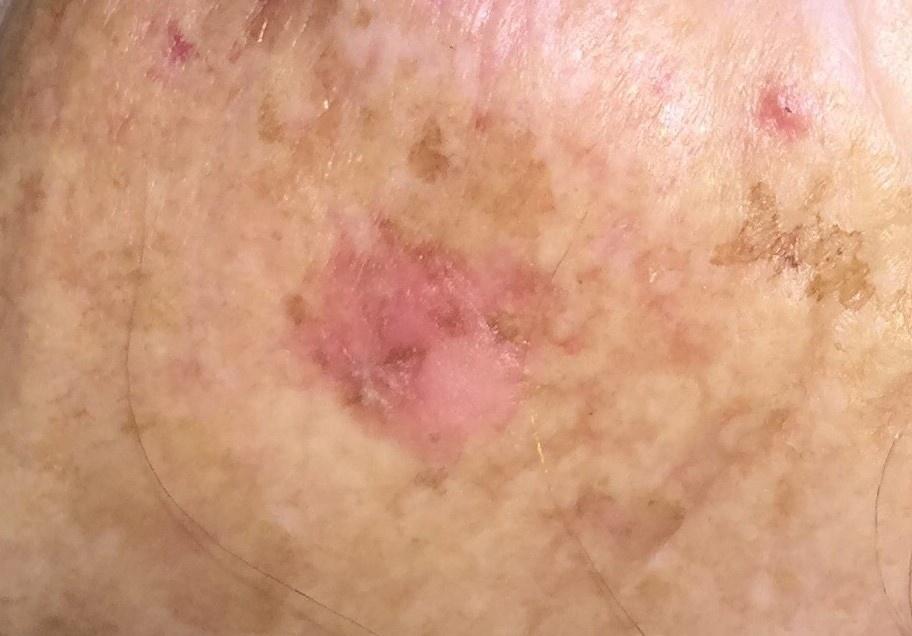patient: female, about 85 years old or older | modality: clinical photograph | body site: the head or neck | diagnostic label: Squamous cell carcinoma (biopsy-proven).